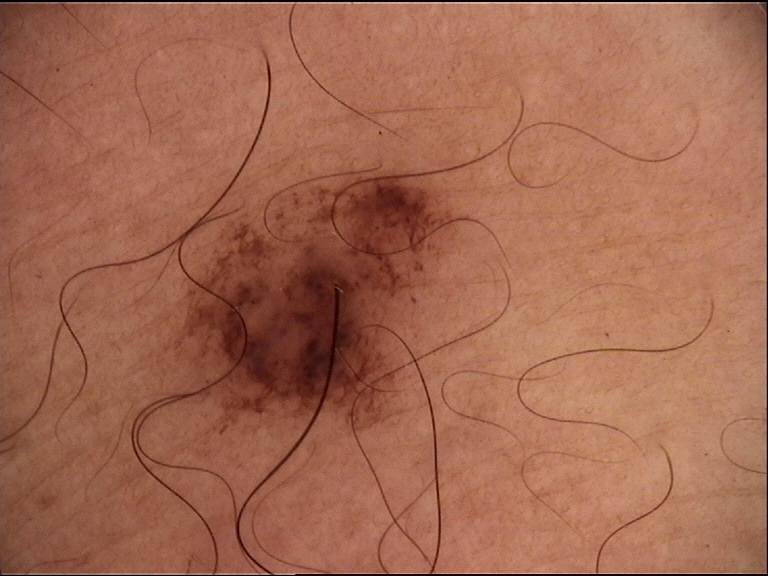* label · dysplastic compound nevus (expert consensus)